This image was taken at a distance · the subject is 50–59, female · the lesion involves the leg:
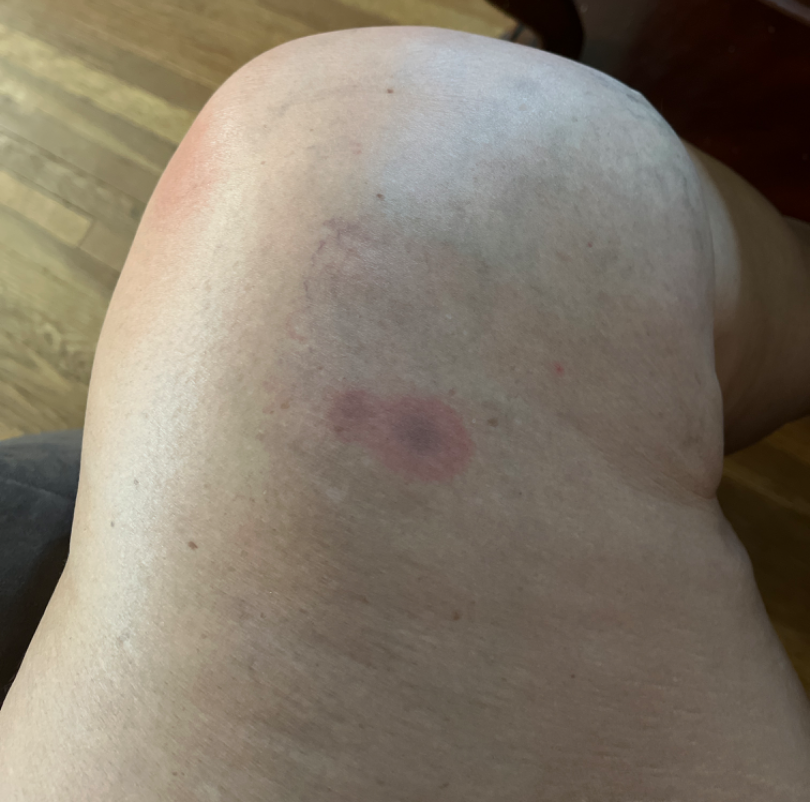The patient indicates enlargement and itching.
Reported duration is one to three months.
The lesion is described as flat.
The patient indicates associated fatigue.
Geographic tongue (0.55); Insect Bite (0.27); Erythema multiforme (0.18).